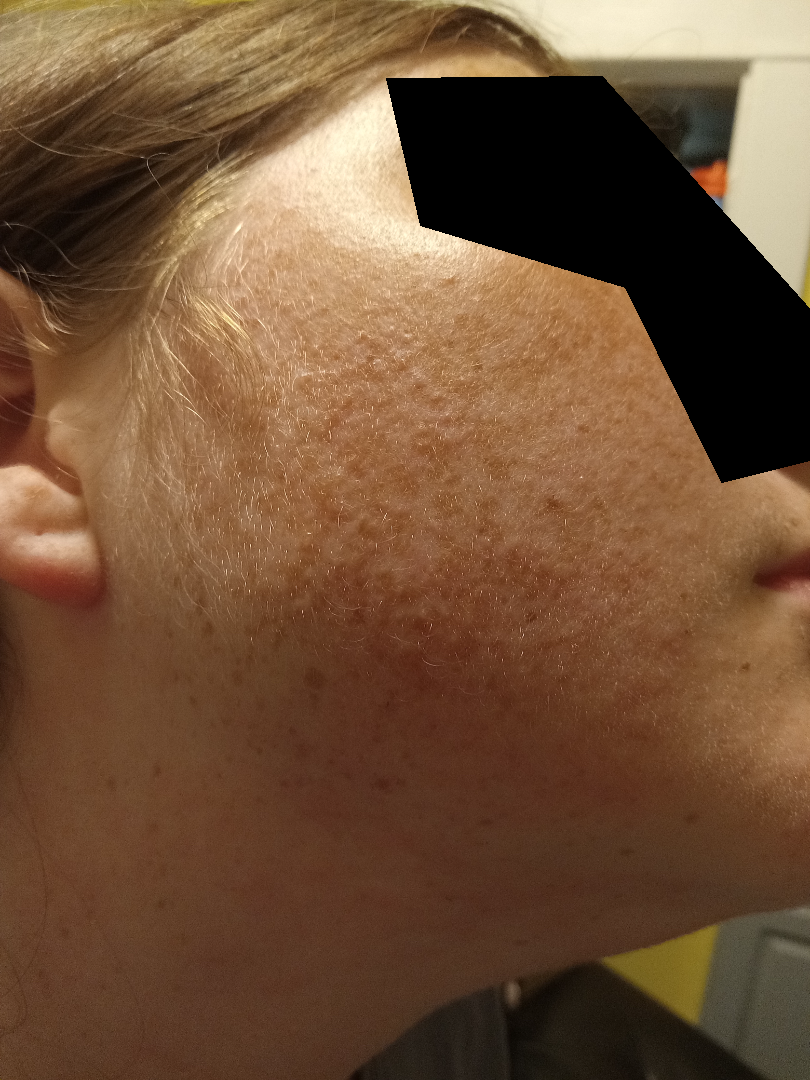skin tone = human graders estimated MST 2 or 3
view = close-up
differential = Acne and Allergic Contact Dermatitis were considered with similar weight